A male patient 83 years old. A dermoscopy image of a skin lesion. Acquired for a research image collection, with no referral diagnosis. The patient says their skin reddens with sun exposure. On a questionnaire the patient reported no family history of skin cancer — 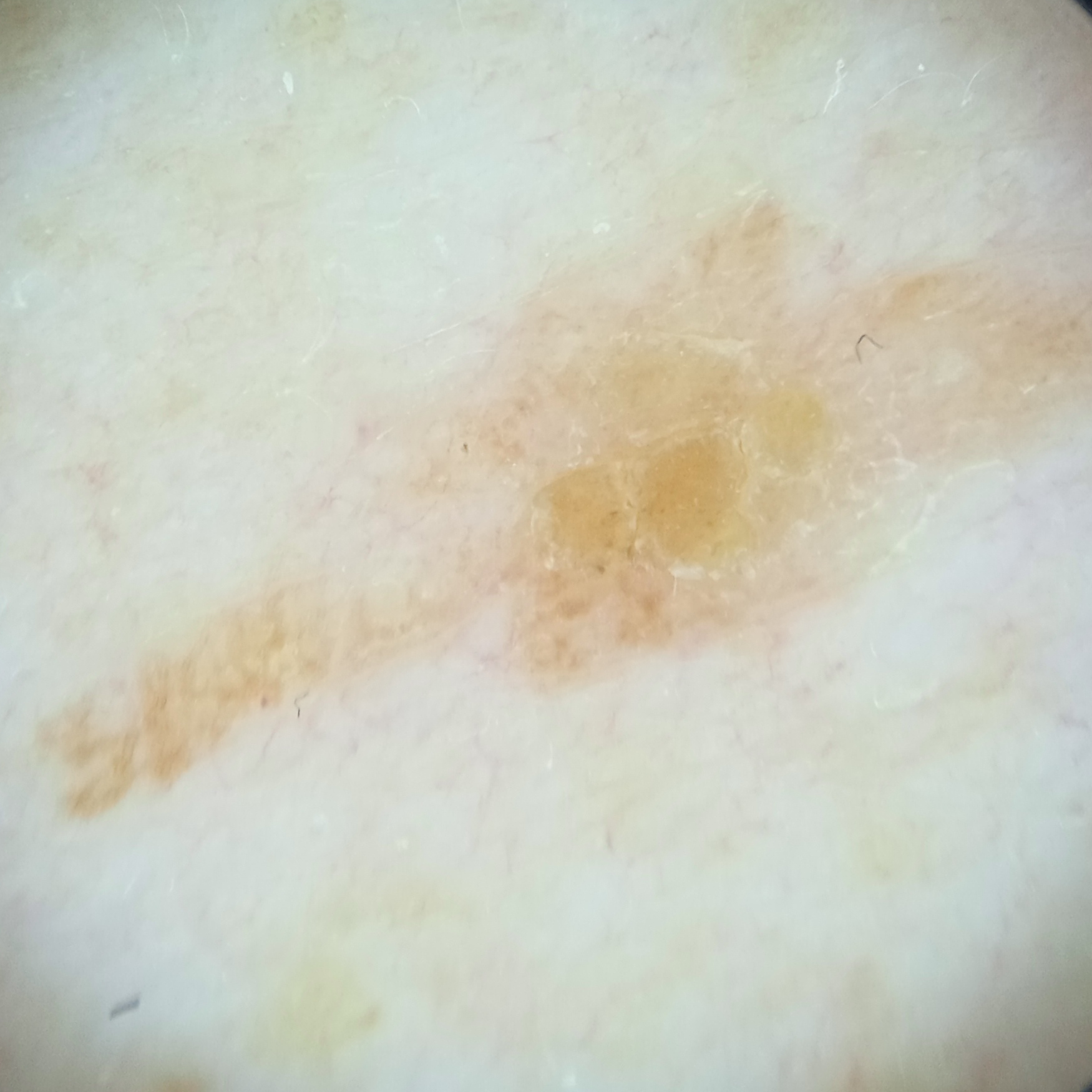Q: What is the anatomic site?
A: the back
Q: What was the diagnosis?
A: seborrheic keratosis (dermatologist consensus)